Symptoms reported: bothersome appearance and itching. The photograph was taken at a distance. The patient considered this a rash. Reported duration is less than one week. The contributor is a male aged 18–29. The contributor notes the lesion is raised or bumpy. No associated systemic symptoms reported. The leg is involved.
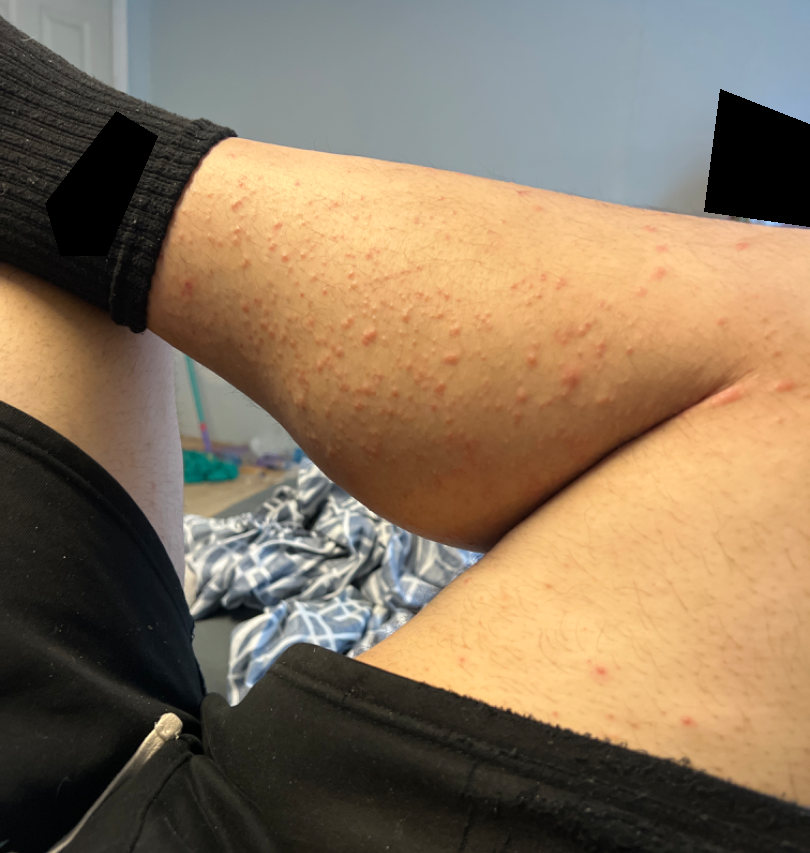On independent review by the dermatologists, Folliculitis (considered); Eczema (considered); Scabies (lower probability); Allergic Contact Dermatitis (lower probability).